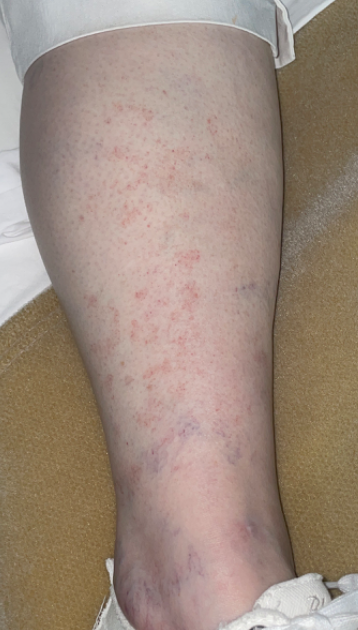Findings:
– location · leg
– patient · female, age 60–69
– framing · at a distance
– clinical impression · most consistent with Pigmented purpuric eruption